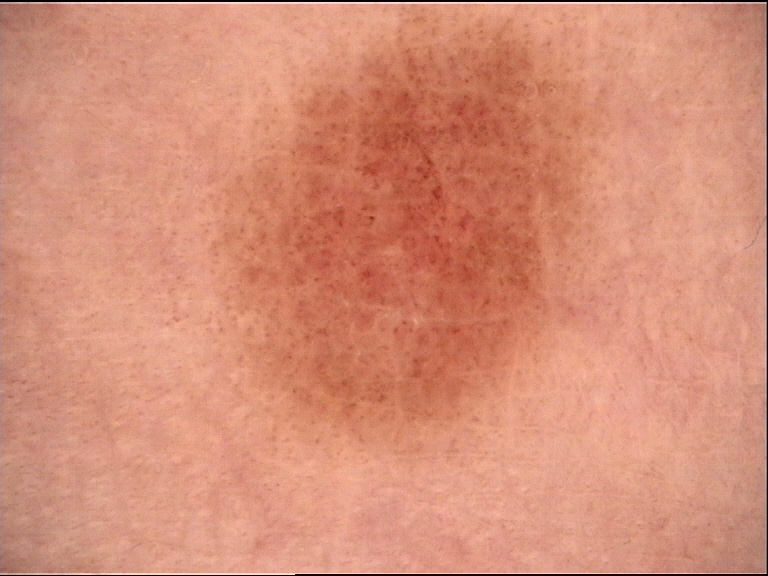A dermoscopy image of a single skin lesion.
Consistent with a benign lesion — a dysplastic compound nevus.